A dermoscopic photograph of a skin lesion: 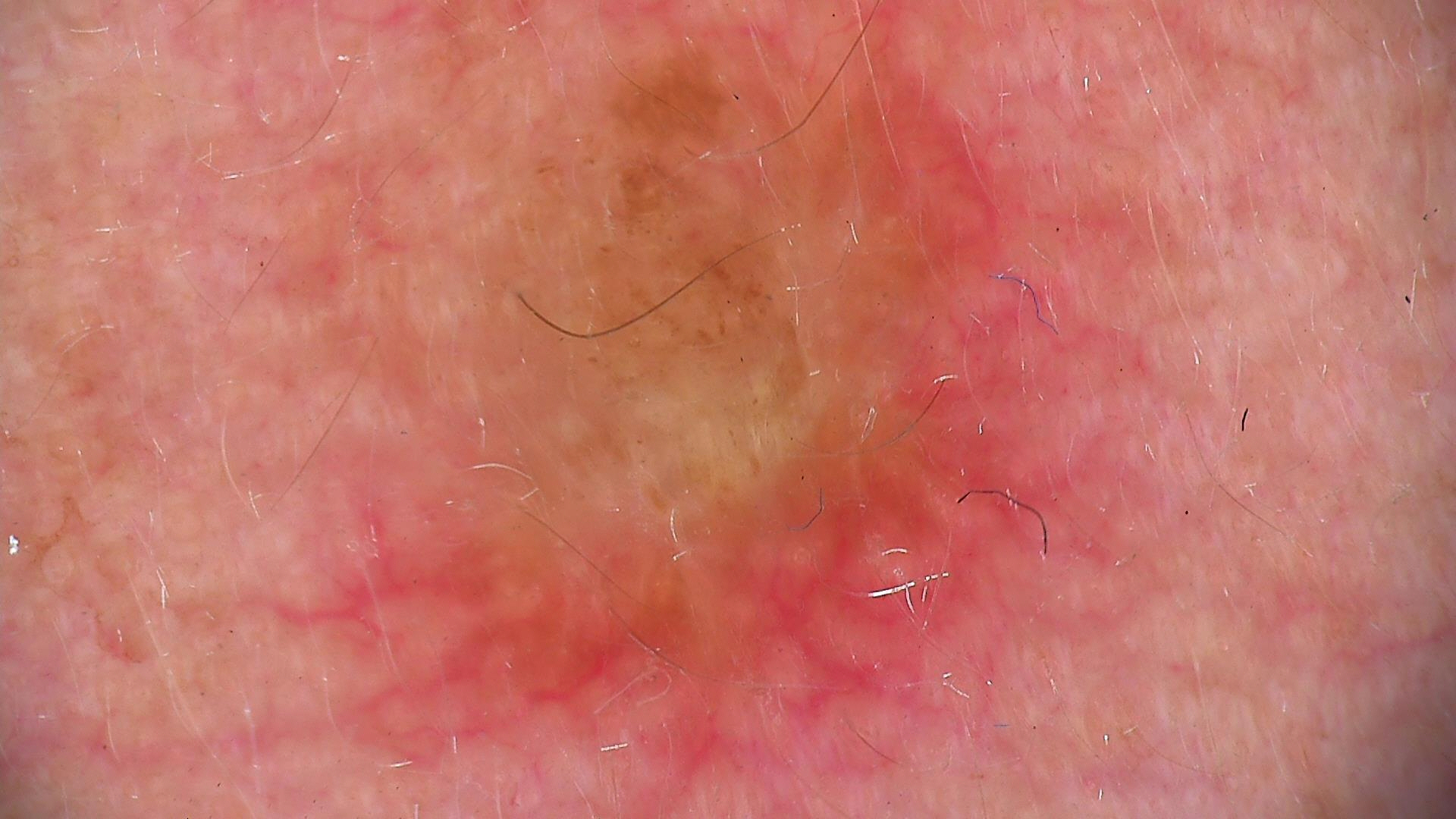Q: What was the diagnostic impression?
A: dermal nevus (expert consensus)